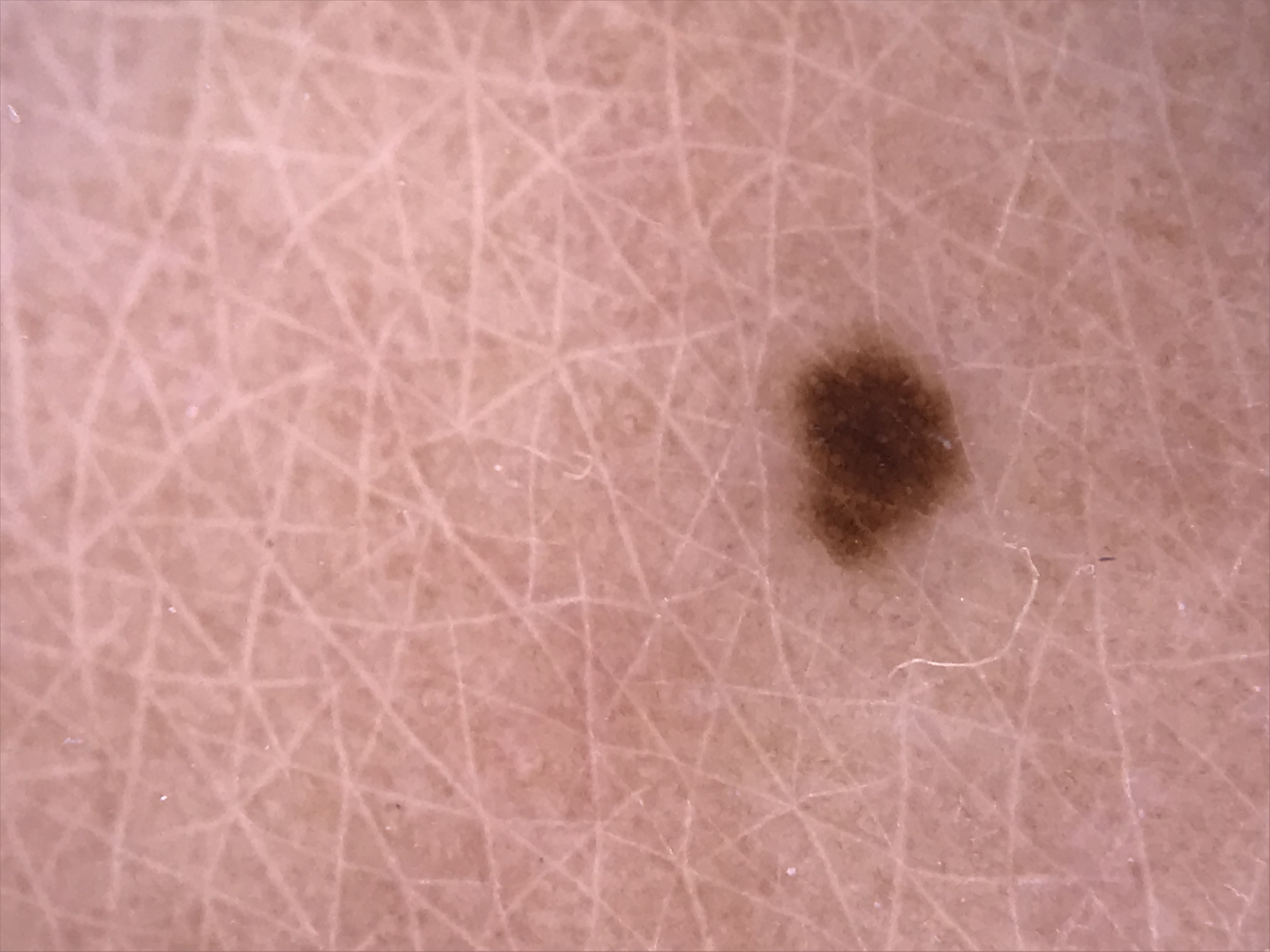A dermatoscopic image of a skin lesion. Classified as a banal lesion — a junctional nevus.